A close-up photograph; located on the leg; male subject, age 18–29: 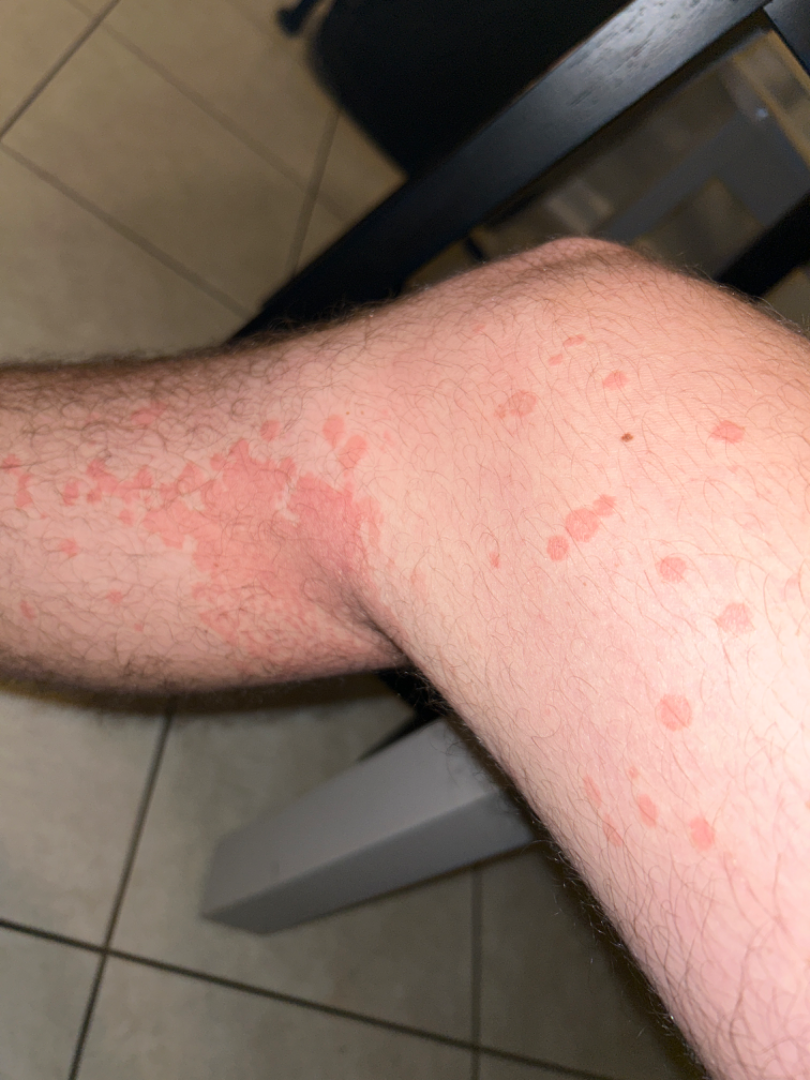Background: The lesion is associated with itching and bothersome appearance. The patient considered this a rash. The patient indicates the condition has been present for about one day. The patient reported no systemic symptoms. The patient indicates the lesion is flat. Findings: Three dermatologists each reviewed the case: Tinea Versicolor and Psoriasis were each considered, in no particular order; a remote consideration is Eczema.